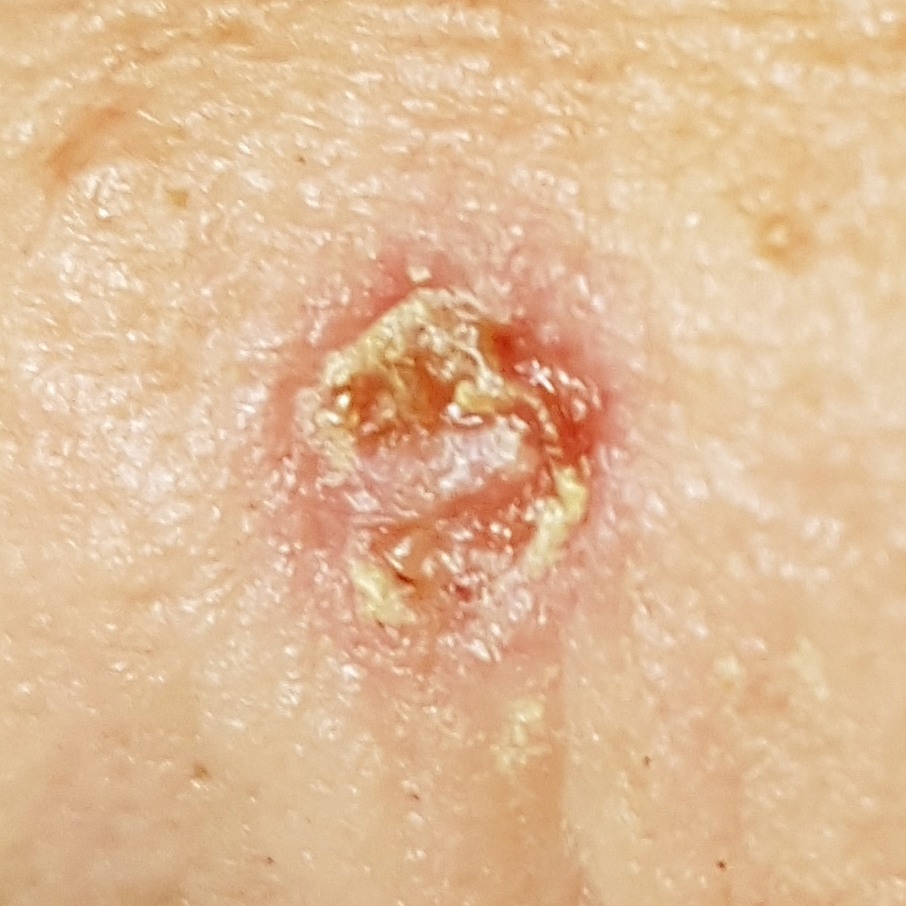Summary:
History notes prior skin cancer (patient or family), tobacco use, pesticide exposure, prior malignancy (patient or family), and alcohol use. A clinical photo of a skin lesion taken with a smartphone. The patient is FST III. The lesion involves the face. The lesion is roughly 5 by 5 mm. Per patient report, the lesion itches, hurts, has bled, and has grown, but has not changed and is not elevated.
Diagnosis:
Biopsy-confirmed as a basal cell carcinoma.